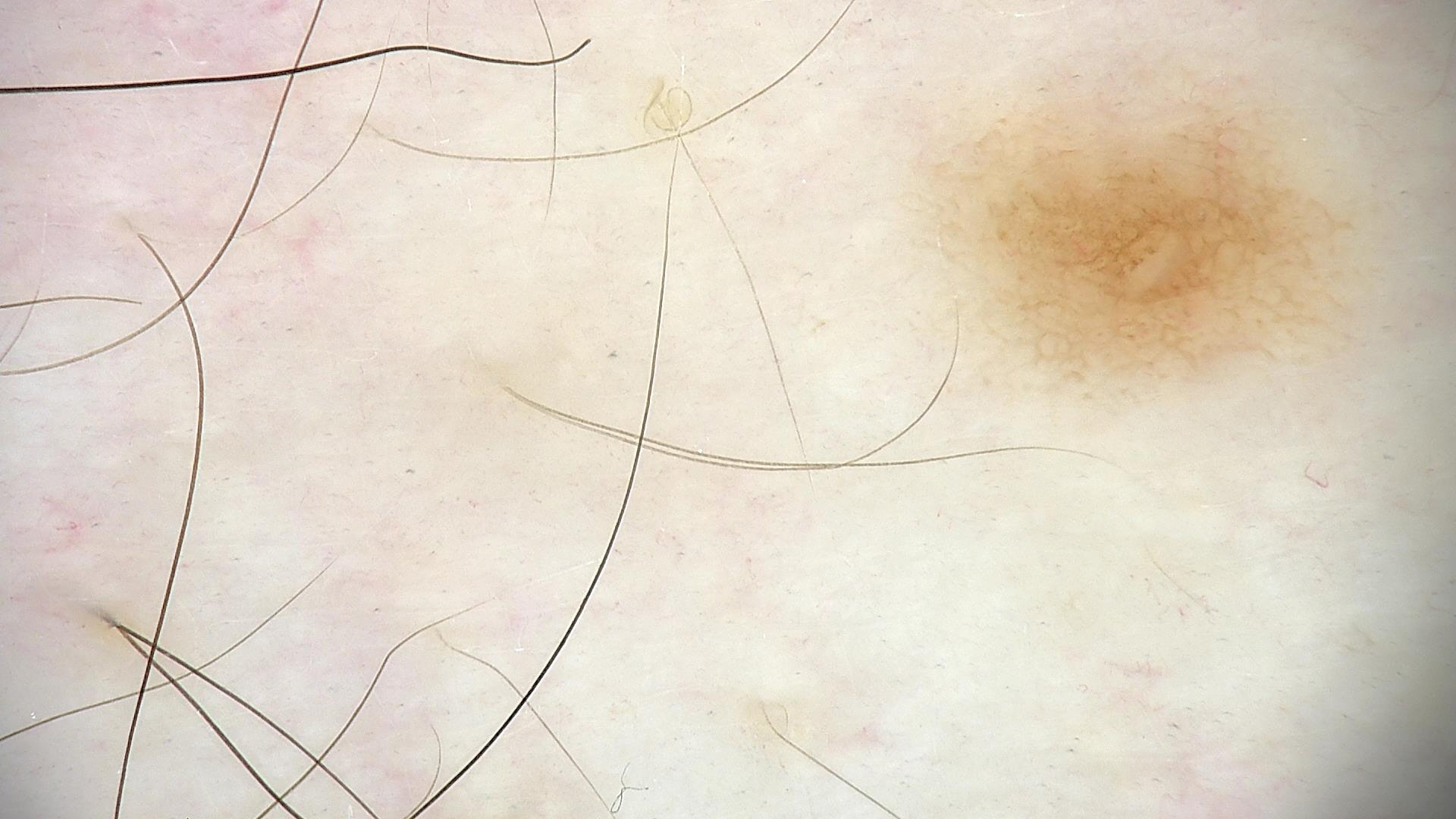A dermoscopic photograph of a skin lesion. The architecture is that of a banal lesion. The diagnosis was a junctional nevus.